A dermoscopic image of a skin lesion · the subject is a male aged 48 to 52.
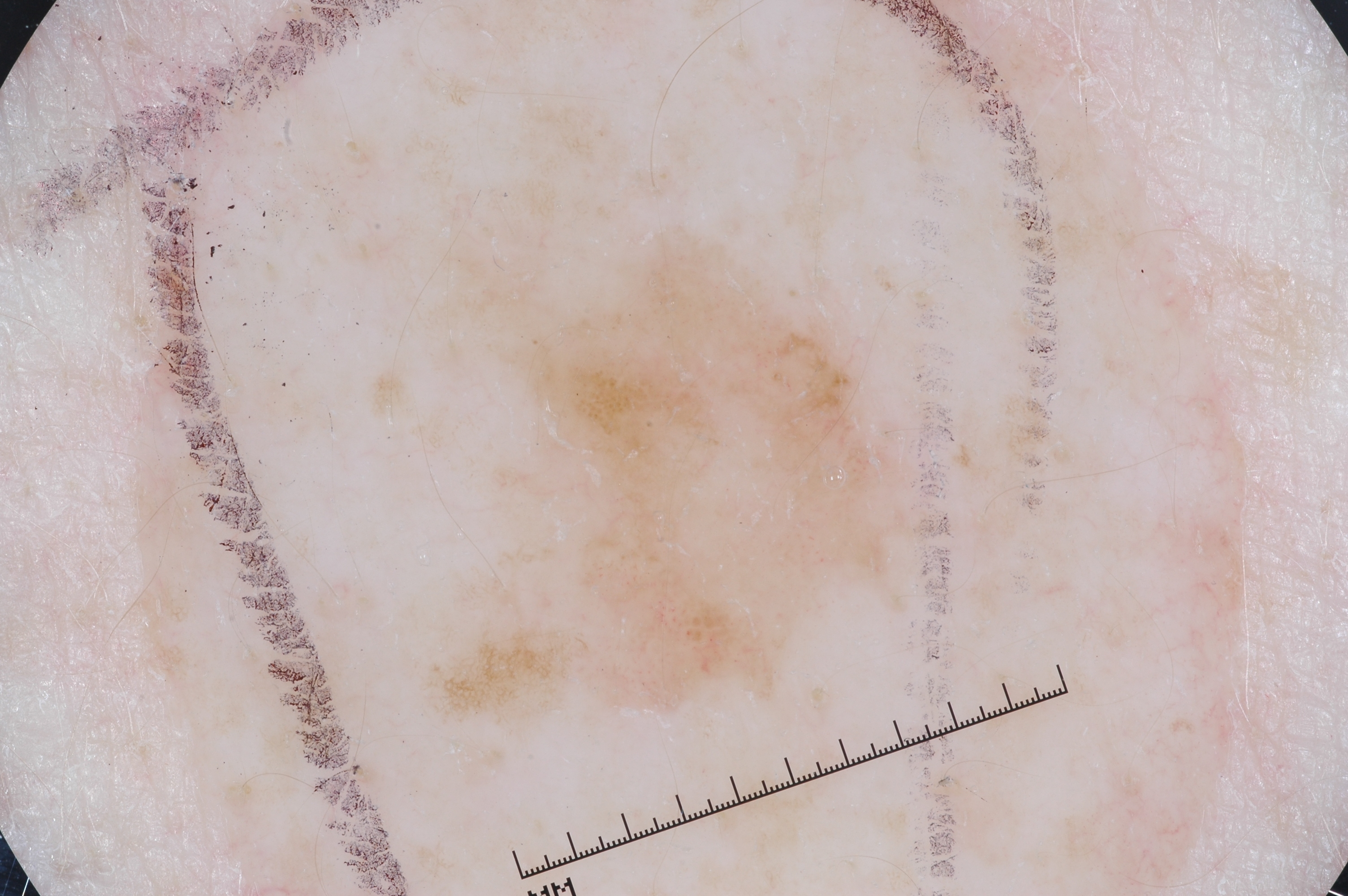Findings:
Dermoscopically, the lesion shows pigment network and milia-like cysts; no negative network or streaks. The lesion is bounded by x1=385, y1=199, x2=937, y2=745.
Impression:
The diagnostic assessment was a melanocytic nevus, a benign skin lesion.